A dermoscopic image of a skin lesion.
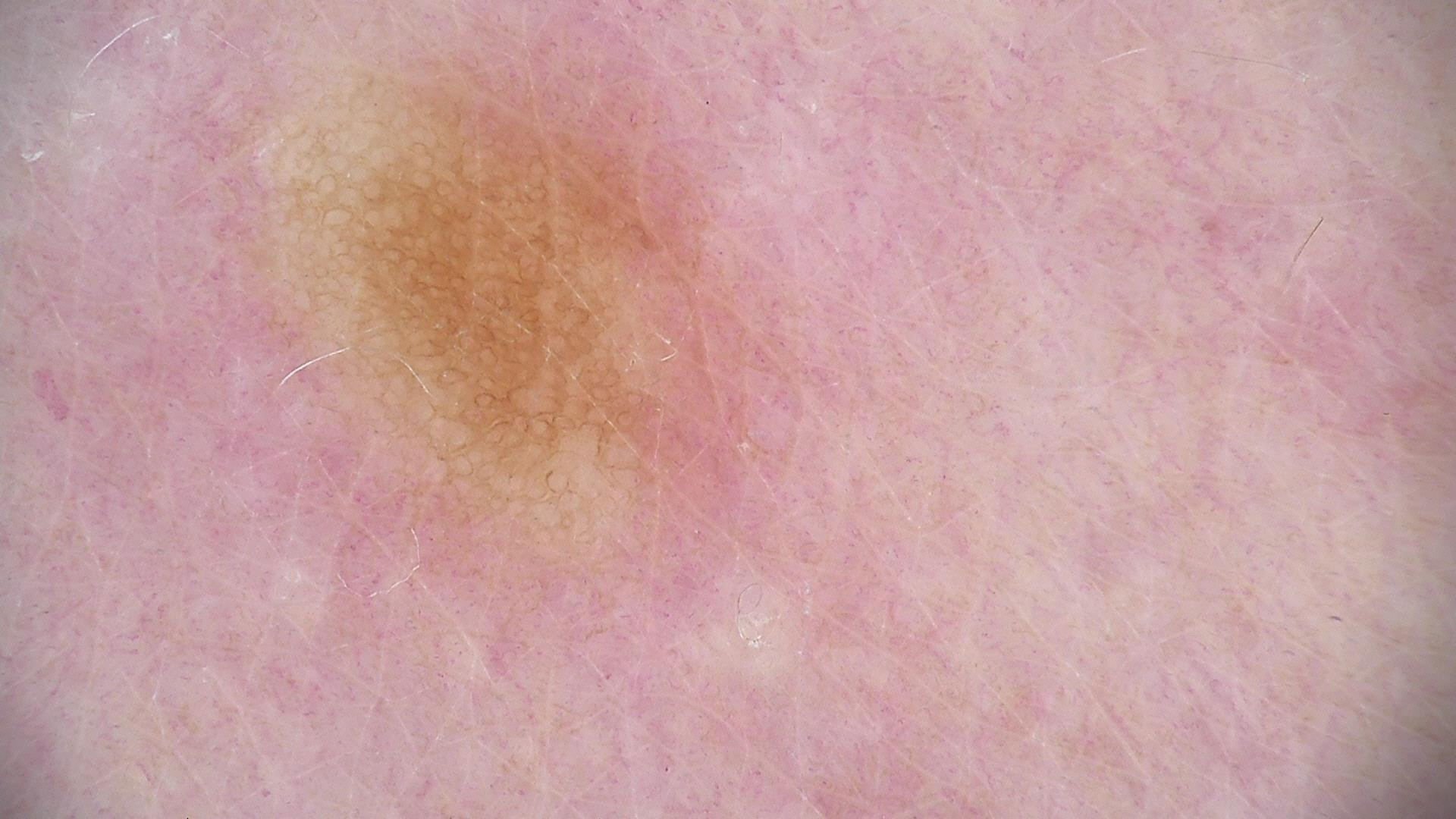Consistent with a benign, fibro-histiocytic lesion — a dermatofibroma.